The patient also reports fatigue and joint pain; the patient reports the condition has been present for more than one year; the patient considered this a rash; a close-up photograph; the patient is 50–59, female; located on the back of the hand, leg and arm — 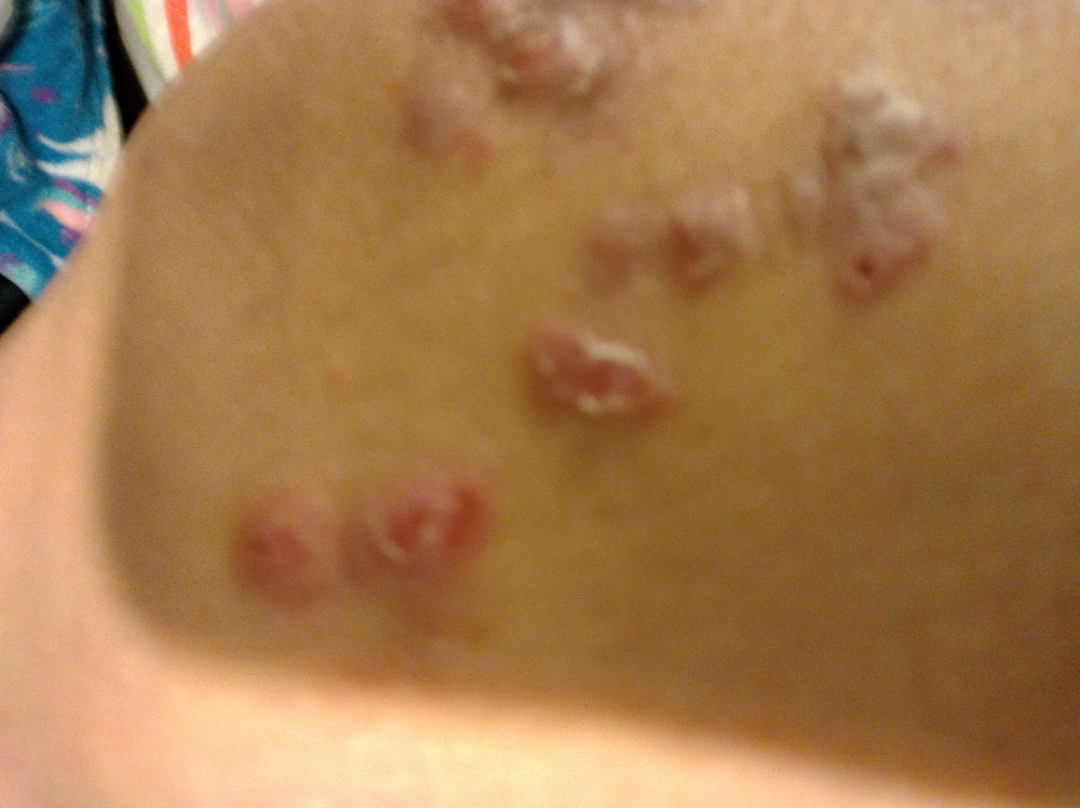Q: Could the case be diagnosed?
A: indeterminate